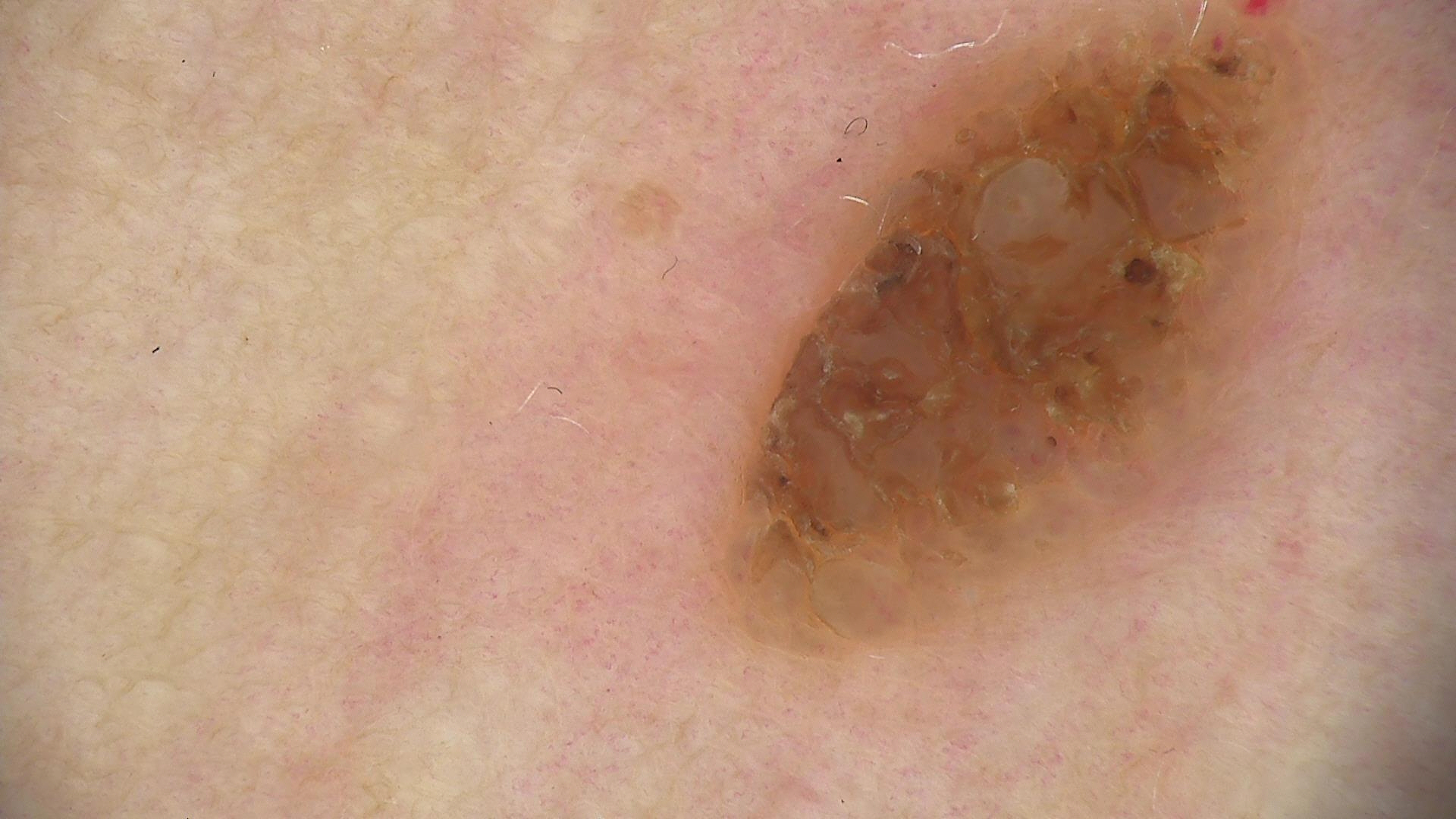Dermoscopy of a skin lesion.
This is a keratinocytic lesion.
Consistent with a benign lesion — a seborrheic keratosis.